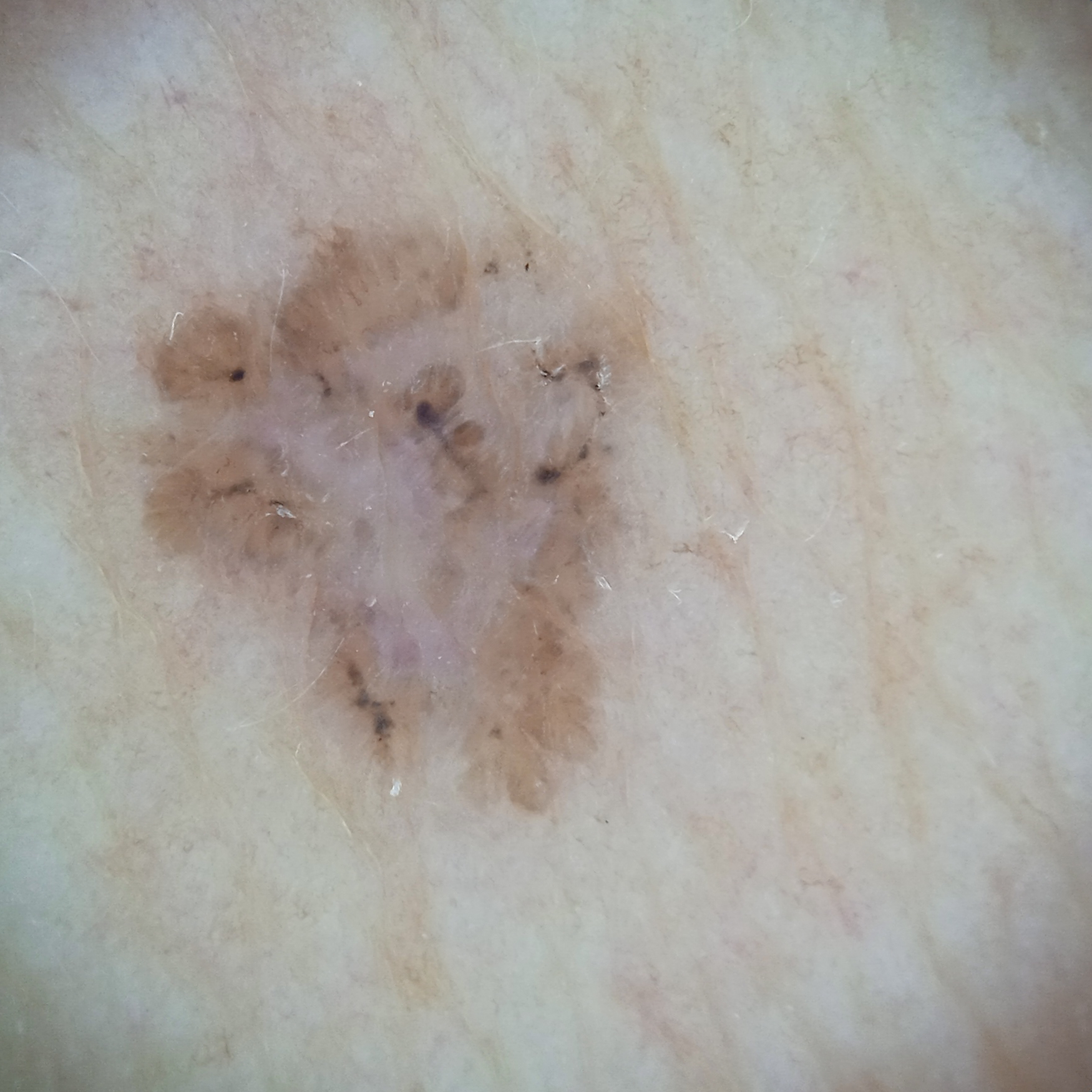Q: What was the diagnosis?
A: basal cell carcinoma (dermatologist consensus)